A male patient, in their mid-40s; a dermoscopic image of a skin lesion.
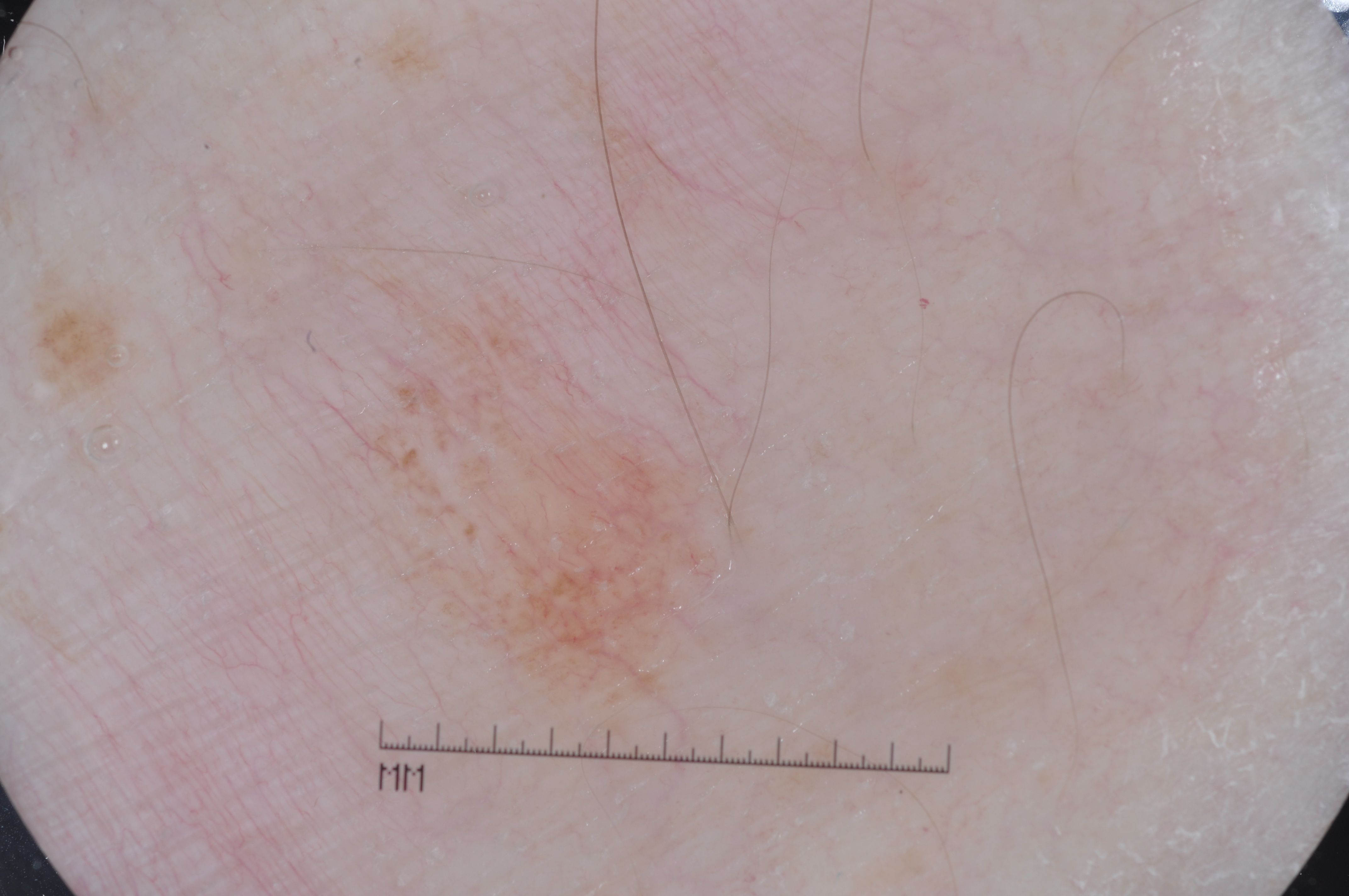Image and clinical context: Dermoscopic examination shows no milia-like cysts, negative network, pigment network, or streaks. In (x1, y1, x2, y2) order, the lesion is bounded by [198, 167, 735, 710]. The lesion covers approximately 15% of the dermoscopic field. Assessment: The clinical diagnosis was a melanocytic nevus.